The subject is a male about 35 years old, dermoscopy of a skin lesion — 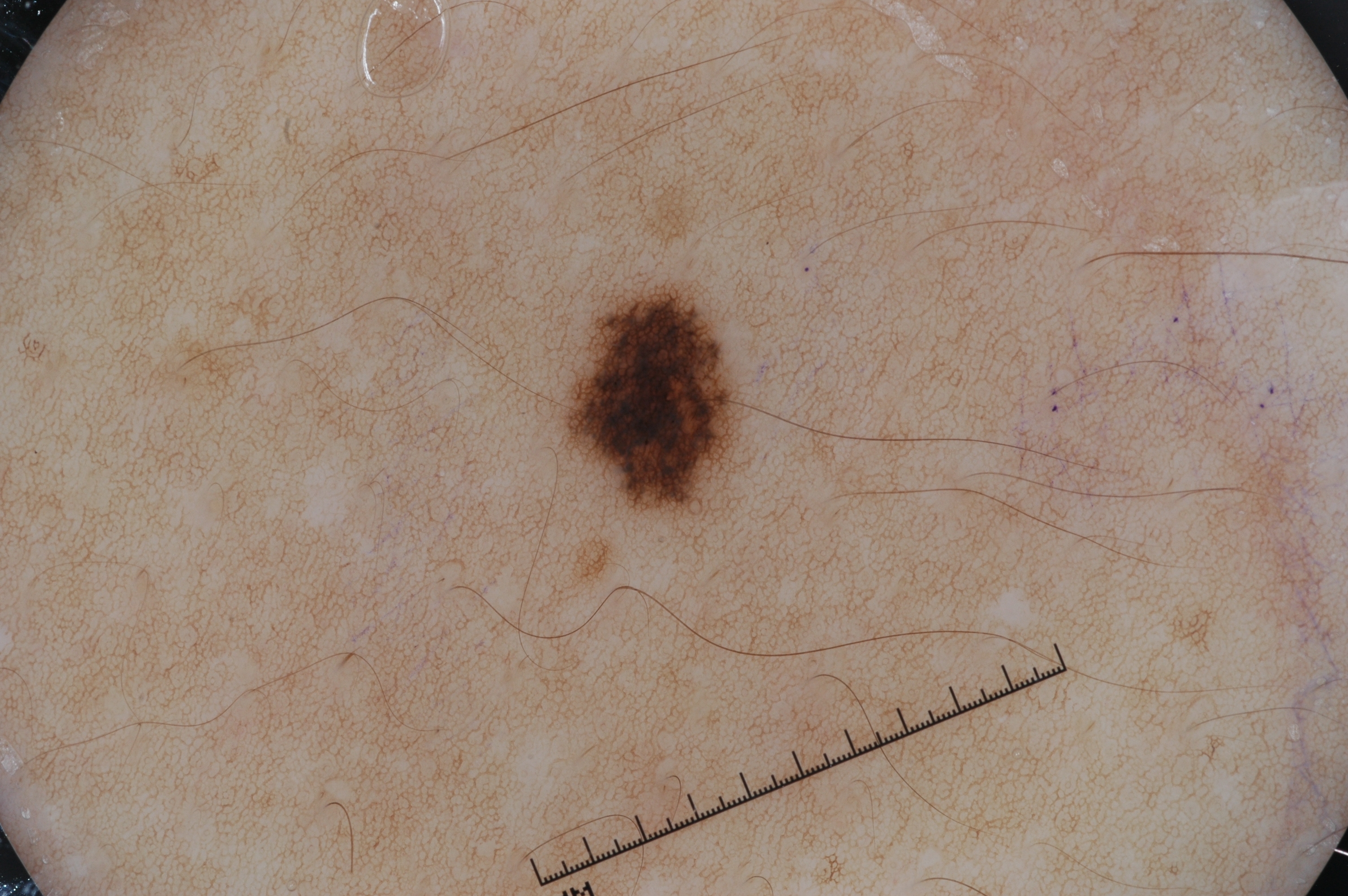Findings:
• extent: small
• dermoscopic pattern: pigment network
• lesion bbox: left=558, top=283, right=747, bottom=522
• impression: a melanocytic nevus, a benign lesion